By history, prior malignancy (patient or family), prior skin cancer (patient or family), and alcohol use — 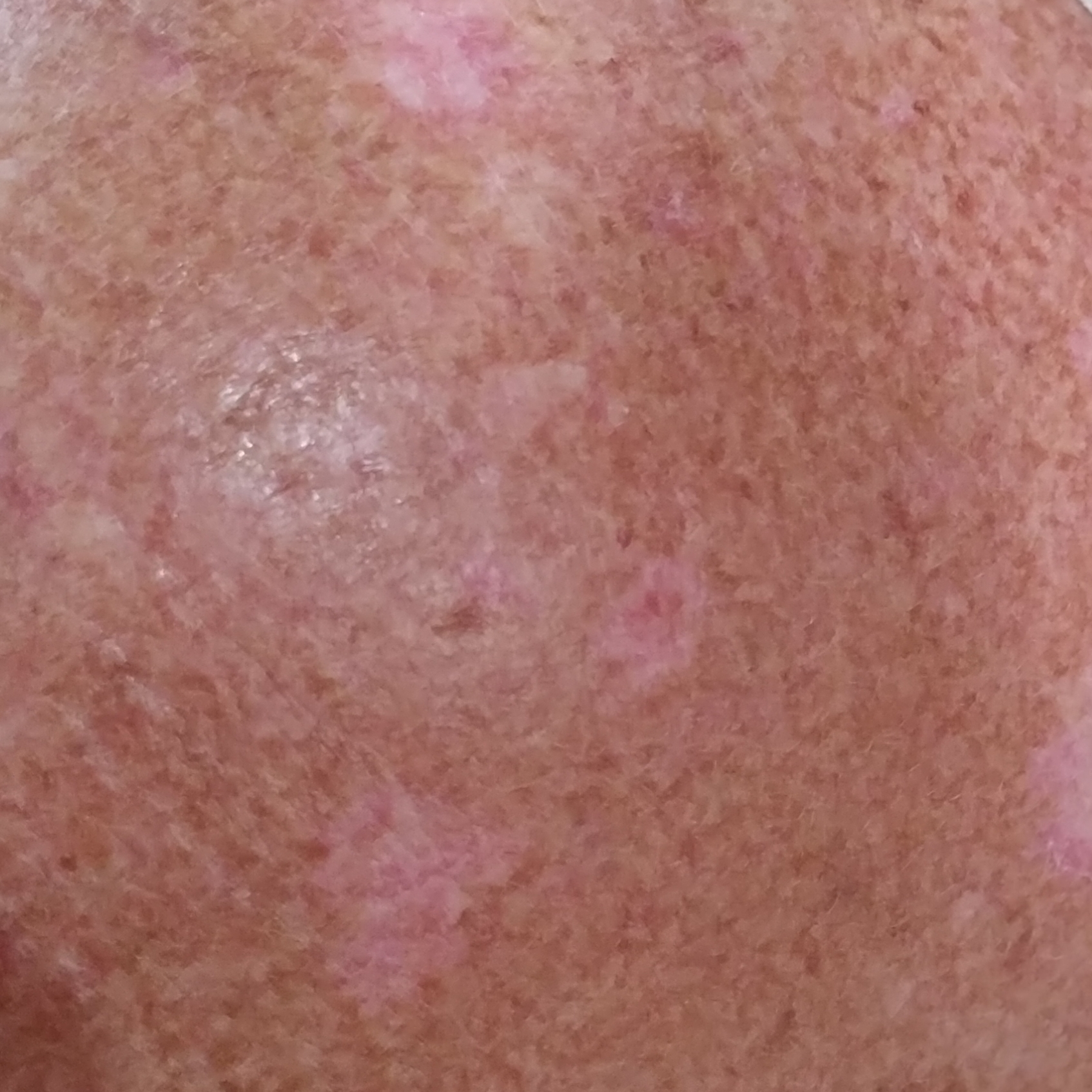By the patient's account, the lesion itches, but has not bled.
Consistent with an actinic keratosis.